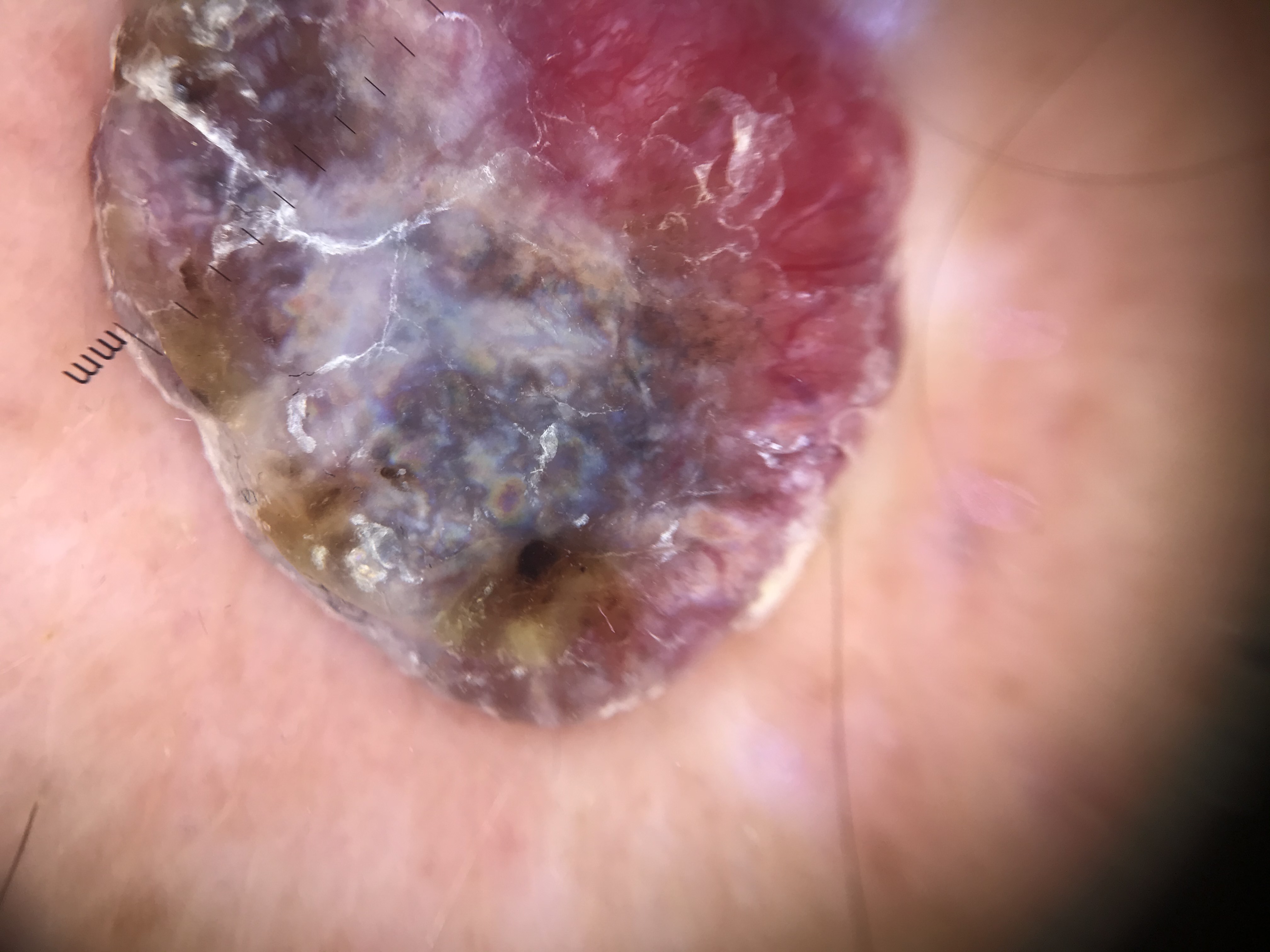A dermoscopic close-up of a skin lesion.
The biopsy diagnosis was a melanoma.